The head or neck is involved · the patient is female · no associated systemic symptoms reported · texture is reported as raised or bumpy and rough or flaky · symptoms reported: burning and itching · the condition has been present for less than one week · the patient considered this a rash · the photograph was taken at a distance: 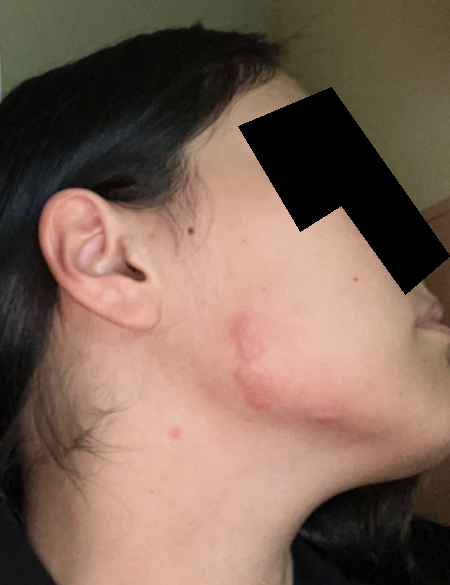On teledermatology review: the leading impression is Scar Condition; also consider Pseudolymphoma; lower on the differential is Urticaria; less likely is Cutaneous lupus.